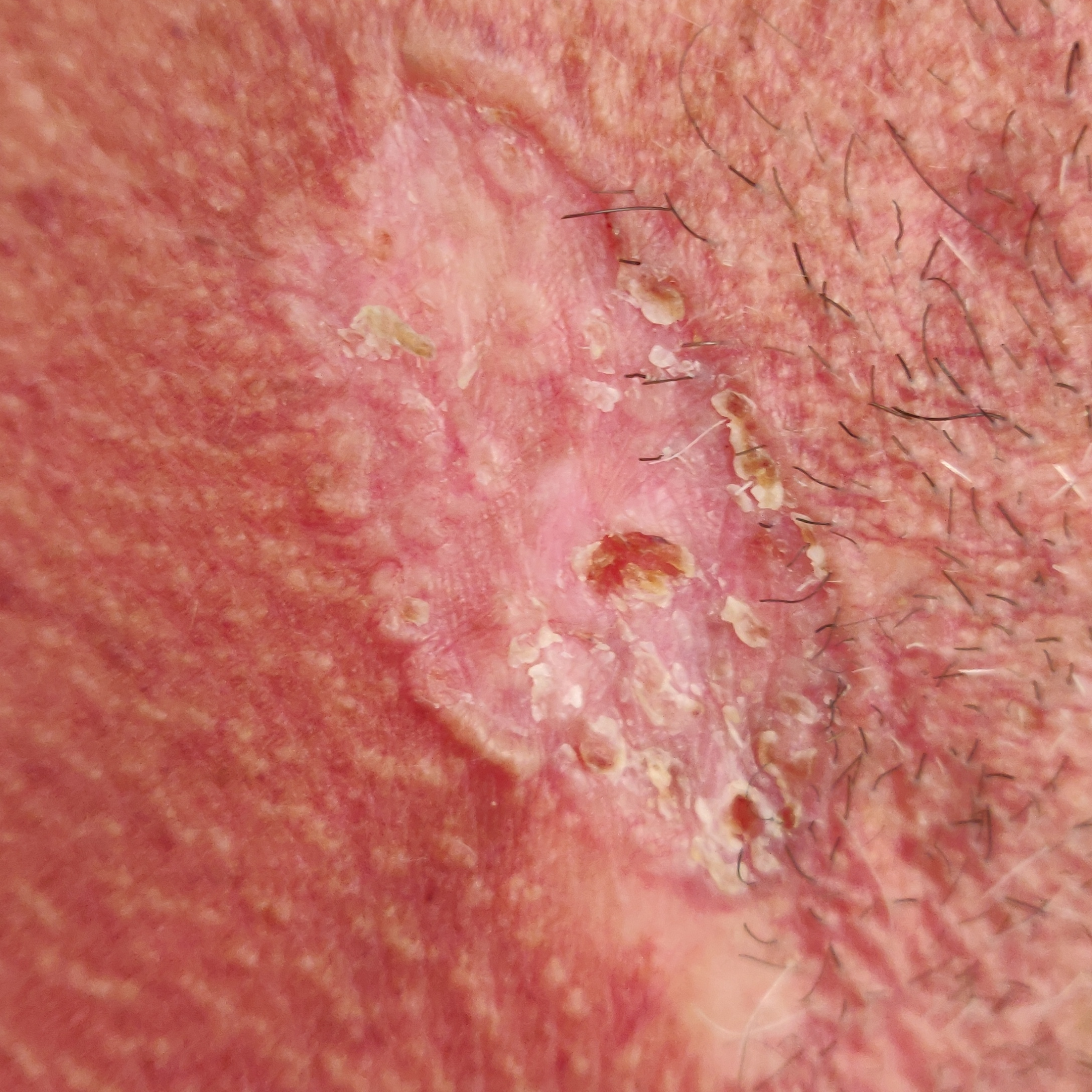Q: Patient demographics?
A: male, age 51
Q: How was this image acquired?
A: clinical photo
Q: Skin phototype?
A: III
Q: What does the exposure history note?
A: pesticide exposure, tobacco use
Q: Where on the body is the lesion?
A: the neck
Q: How large is the lesion?
A: 42 × 21 mm
Q: What does the patient describe?
A: growth, bleeding, itching, elevation / no pain
Q: What did the workup show?
A: basal cell carcinoma (biopsy-proven)